A male patient 65 years old. Referred for assessment of suspected basal cell carcinoma:
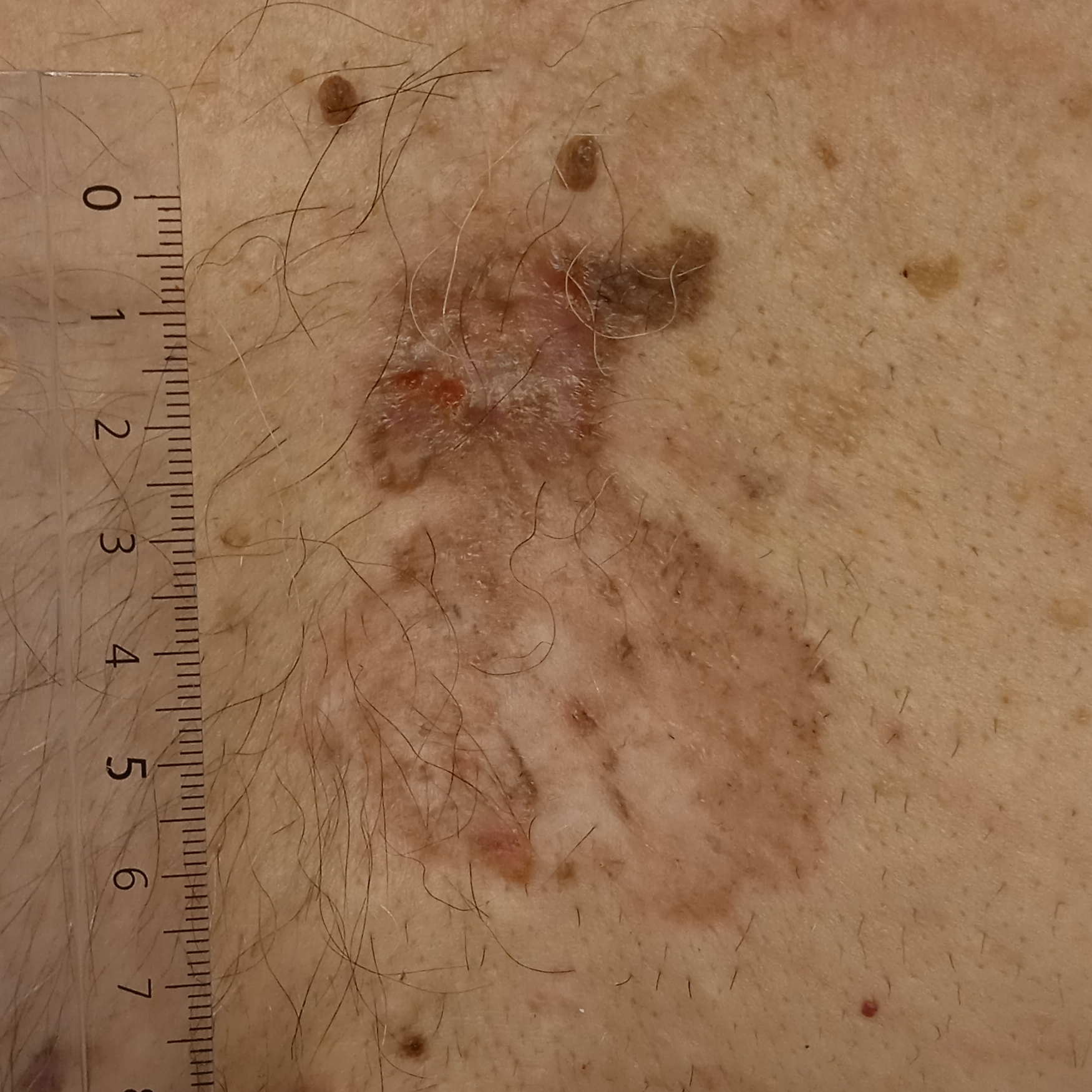anatomic site: the torso, lesion size: 66 mm, pathology: basal cell carcinoma (biopsy-proven).